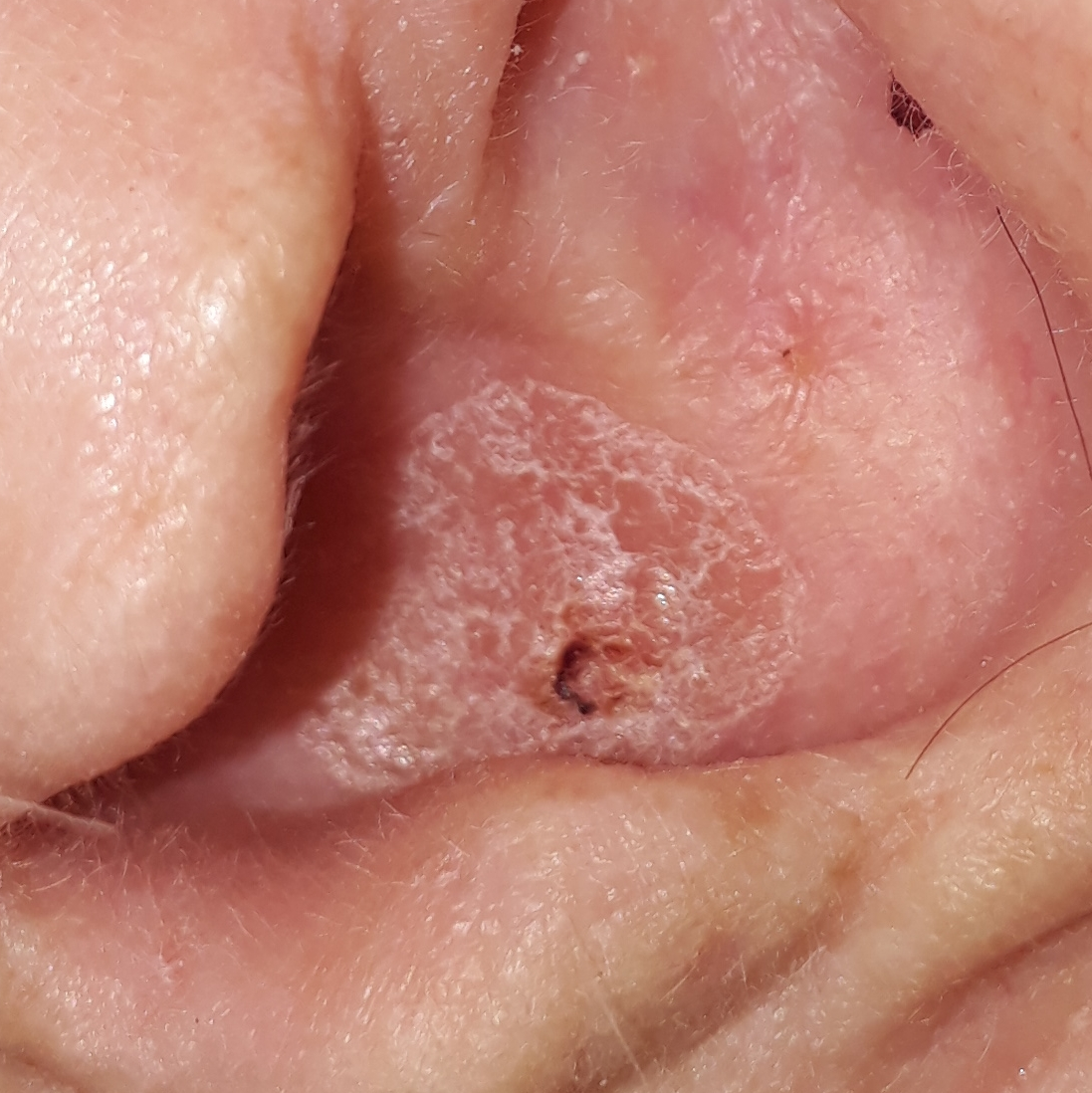History notes prior malignancy (patient or family). A smartphone photograph of a skin lesion. A female patient 77 years of age. The lesion is located on an ear. On biopsy, the diagnosis was a seborrheic keratosis.